Close-up view.
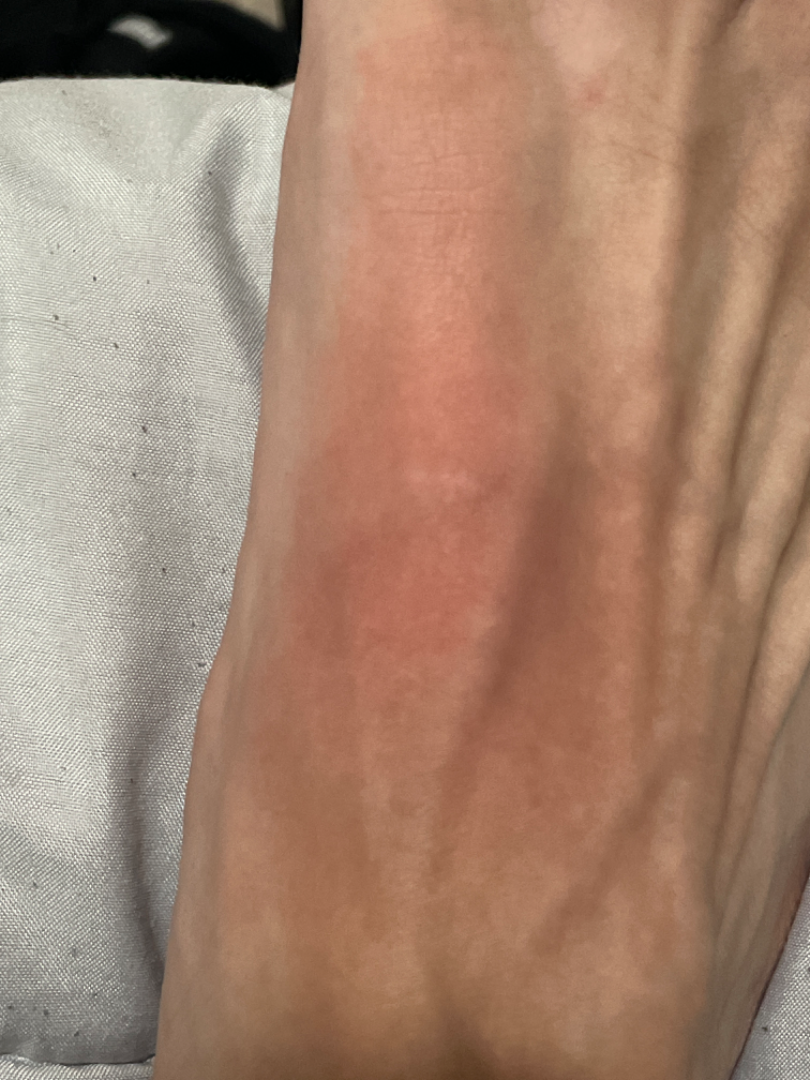The case was difficult to assess from the available photograph.